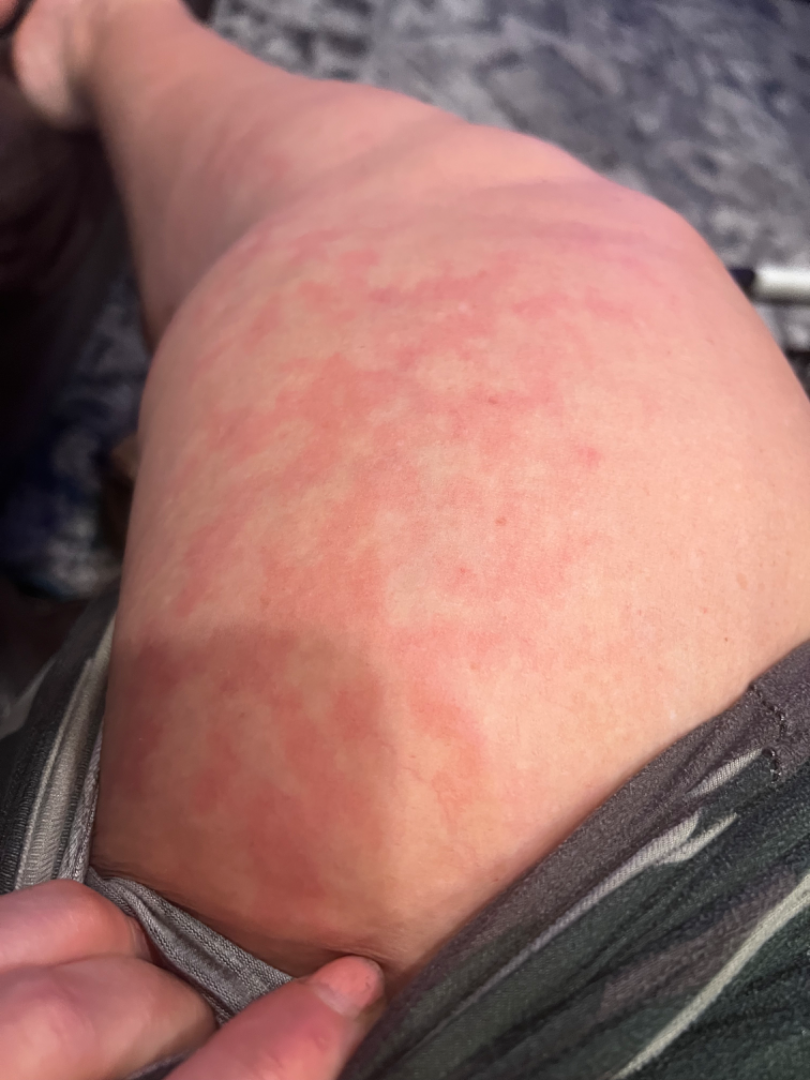The skin condition could not be confidently assessed from this image. The lesion involves the leg. The photograph is a close-up of the affected area.